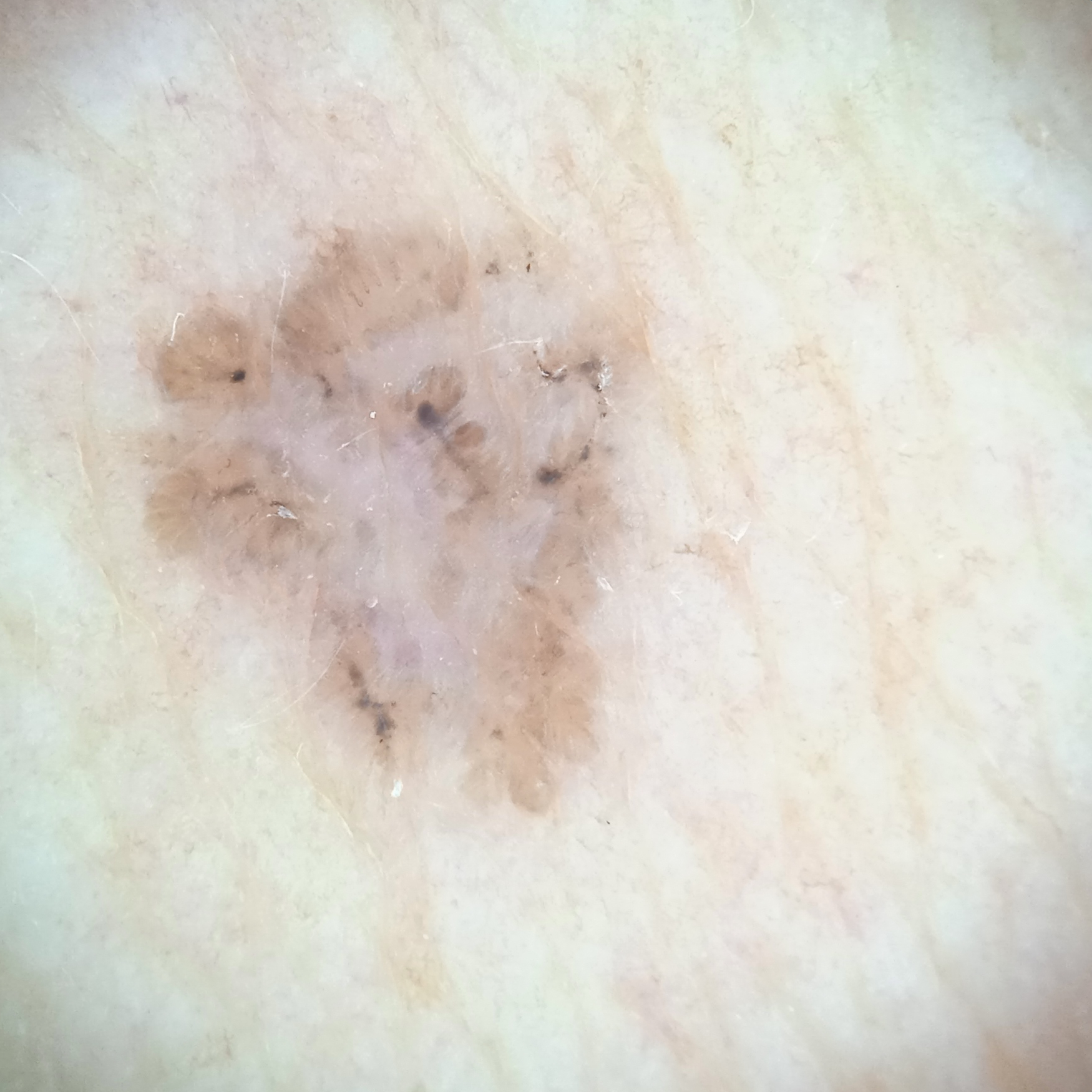| feature | finding |
|---|---|
| subject | female, 60 years old |
| relevant history | a personal history of skin cancer, a personal history of cancer, no family history of skin cancer |
| image | dermoscopy |
| sun reaction | skin tans without first burning |
| referral context | clinical suspicion of basal cell carcinoma |
| diagnosis | basal cell carcinoma (dermatologist consensus) |